A subject 71 years old · a clinical close-up photograph of a skin lesion:
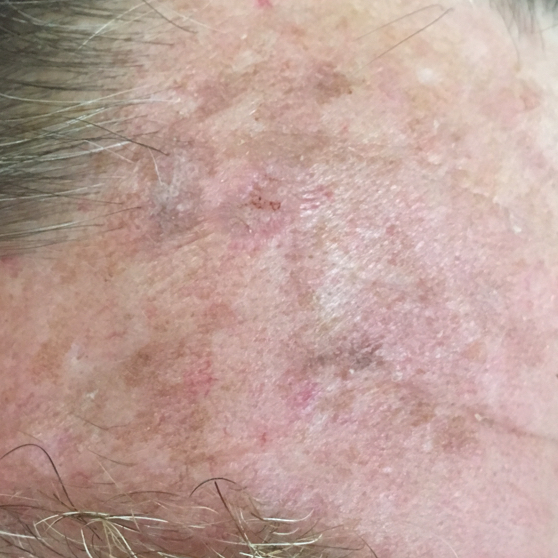Located on the face.
The patient reports that the lesion itches.
Expert review favored a premalignant lesion — an actinic keratosis.